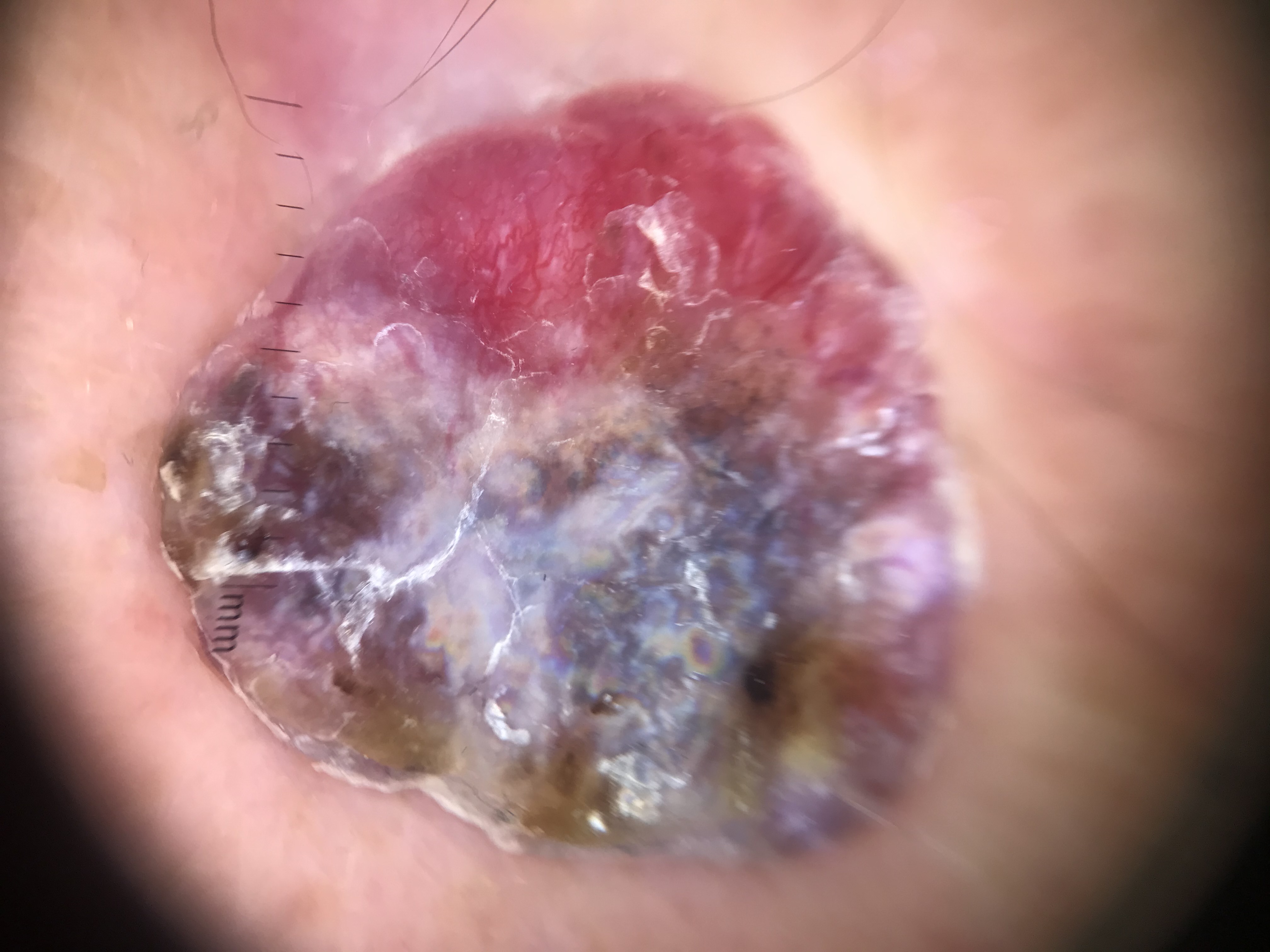Biopsy-confirmed as a melanoma.